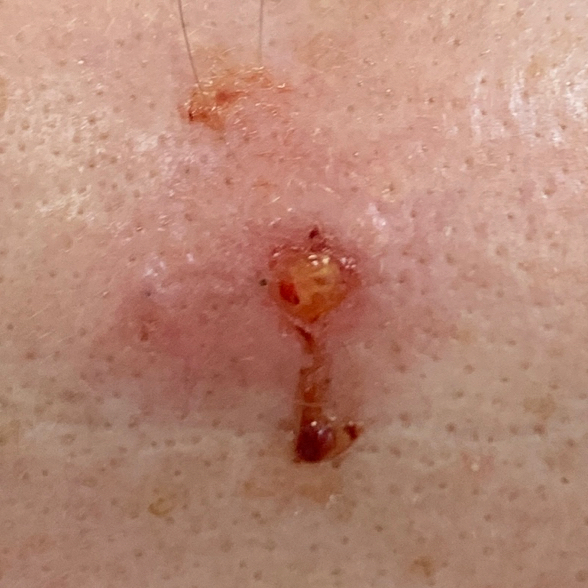A smartphone photograph of a skin lesion. A female patient in their early 50s. By the patient's account, the lesion is elevated, has bled, hurts, and itches. Histopathology confirmed a basal cell carcinoma.